Dermoscopy of a skin lesion: 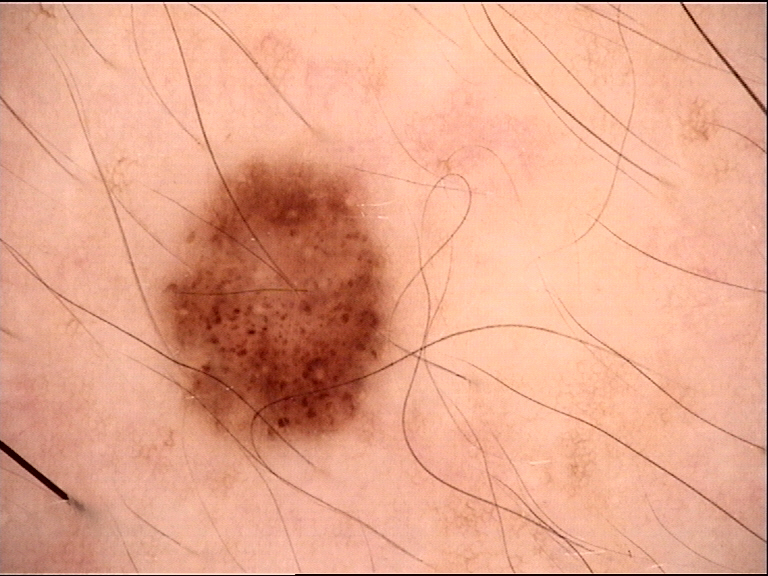Consistent with a dysplastic junctional nevus.